The patient says their skin reddens with sun exposure · referred for assessment of suspected melanocytic nevus · a female patient aged 15 · a dermoscopy image of a skin lesion · few moles overall by the patient's own estimate.
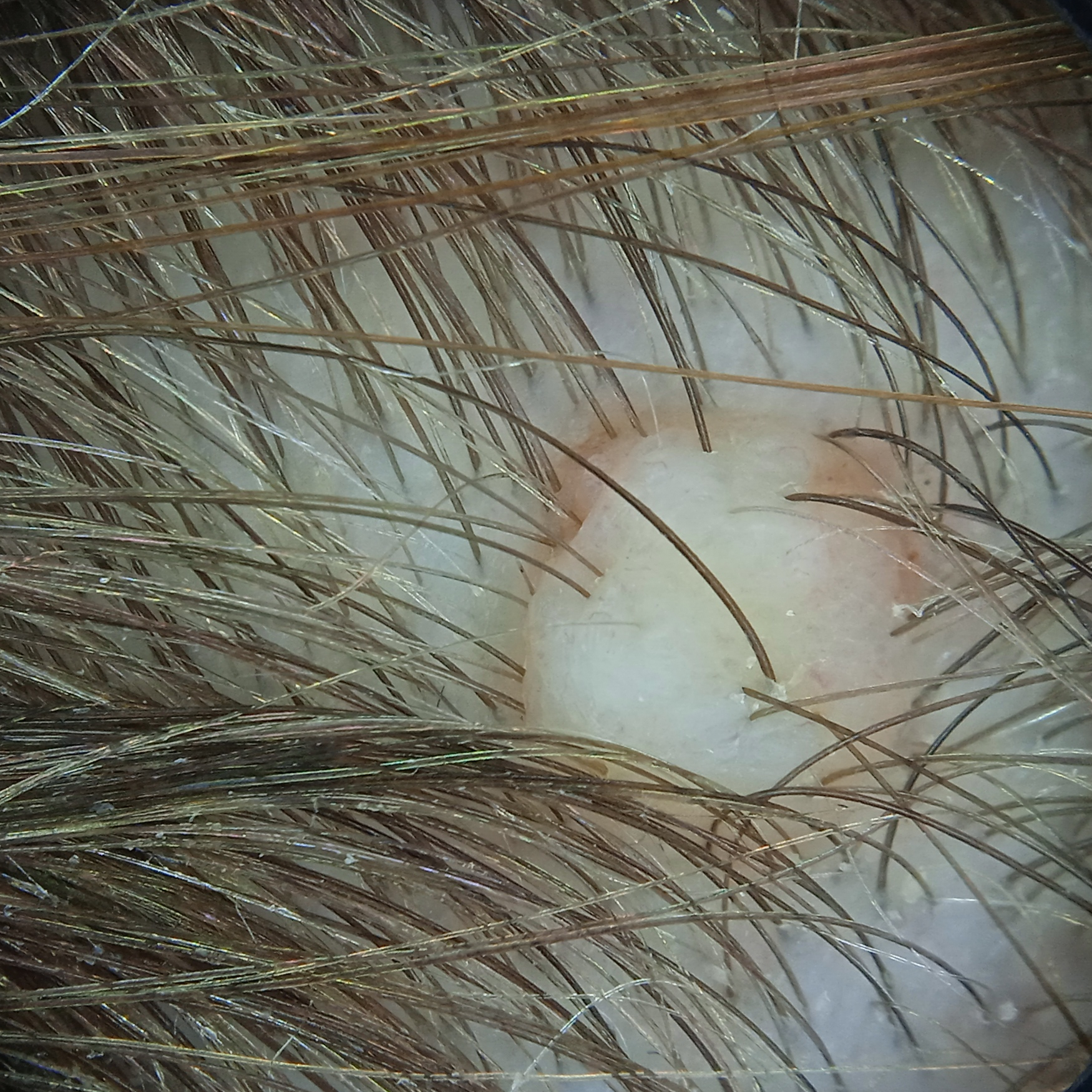  lesion_location: the head
  lesion_size:
    diameter_mm: 5.0
  diagnosis:
    name: melanocytic nevus
    malignancy: benign
    procedure: excision